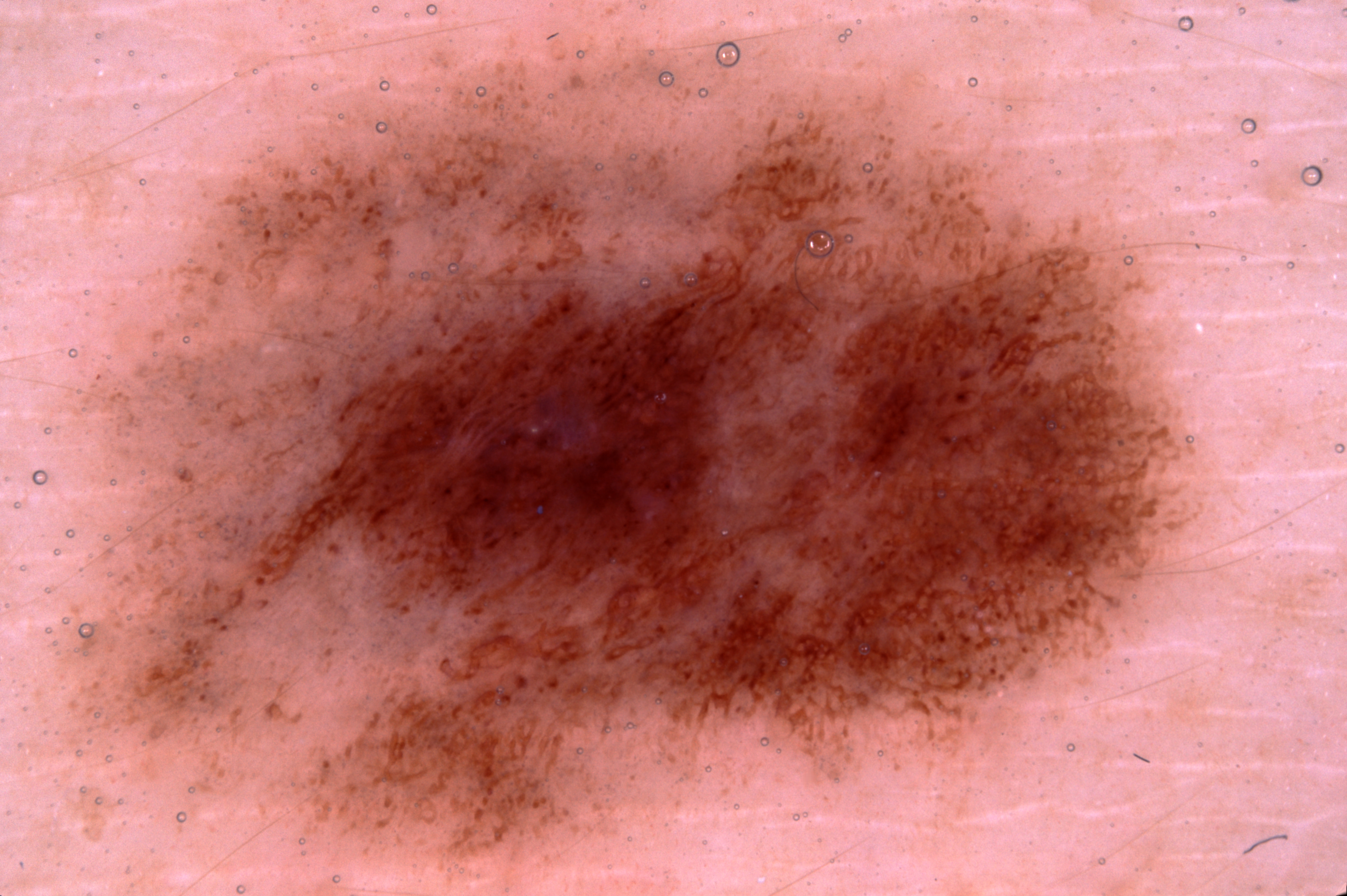A dermatoscopic image of a skin lesion. A female patient aged 23 to 27. The lesion takes up about 57% of the image. As (left, top, right, bottom), the lesion's extent is [99, 47, 1194, 865]. Dermoscopic assessment notes milia-like cysts and pigment network, with no streaks or negative network. The clinical diagnosis was a melanocytic nevus.